A dermatoscopic image of a skin lesion:
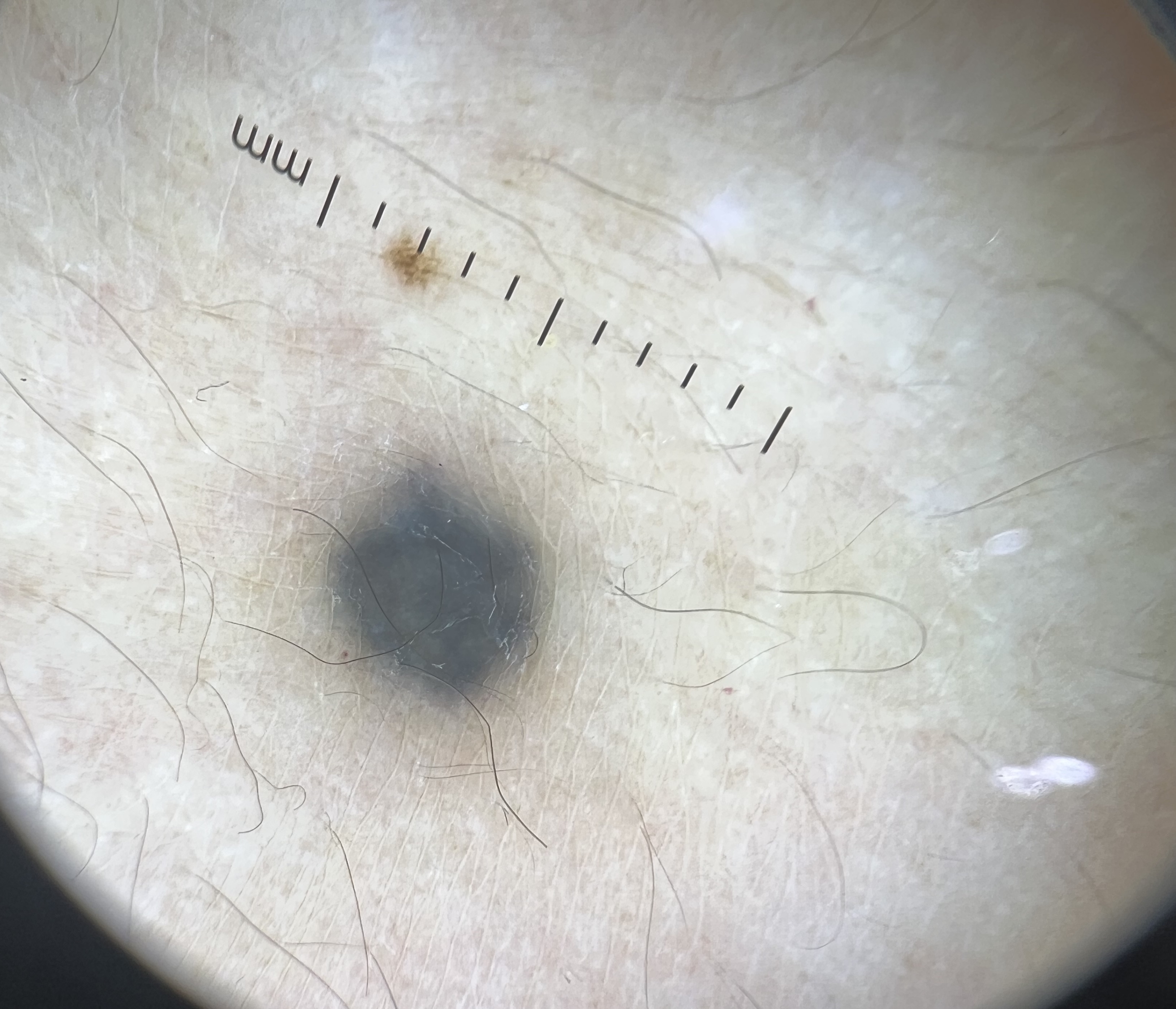  lesion_type:
    main_class: banal
    pattern: dermal
  diagnosis:
    name: blue nevus
    code: bdb
    malignancy: benign
    super_class: melanocytic
    confirmation: expert consensus